A dermoscopic close-up of a skin lesion.
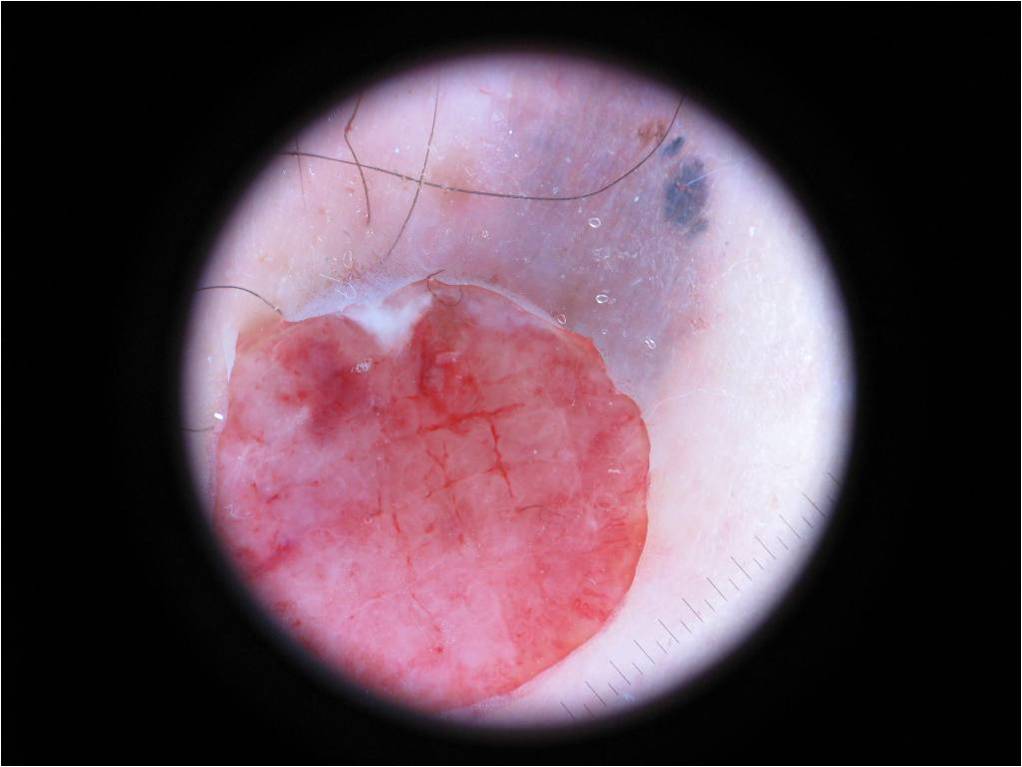With coordinates (x1, y1, x2, y2), the lesion is located at bbox=[181, 57, 718, 717]. Histopathology confirmed a melanoma.